A male subject, about 85 years old or older · a dermoscopic close-up of a skin lesion:
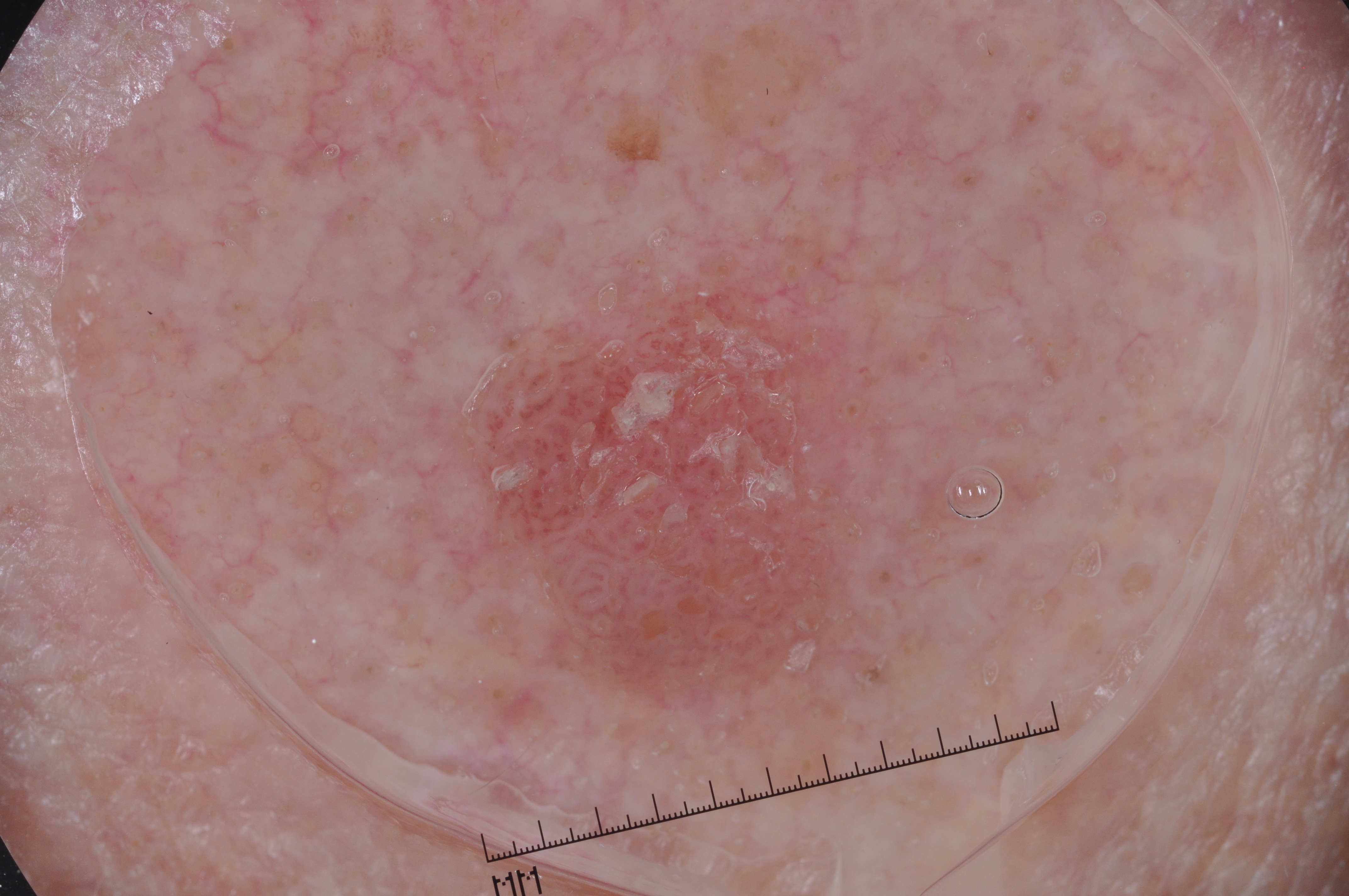Dermoscopic examination shows milia-like cysts; no streaks, pigment network, or negative network. A moderately sized lesion. The lesion occupies the region <bbox>464, 281, 875, 707</bbox>. Consistent with a seborrheic keratosis, a benign skin lesion.